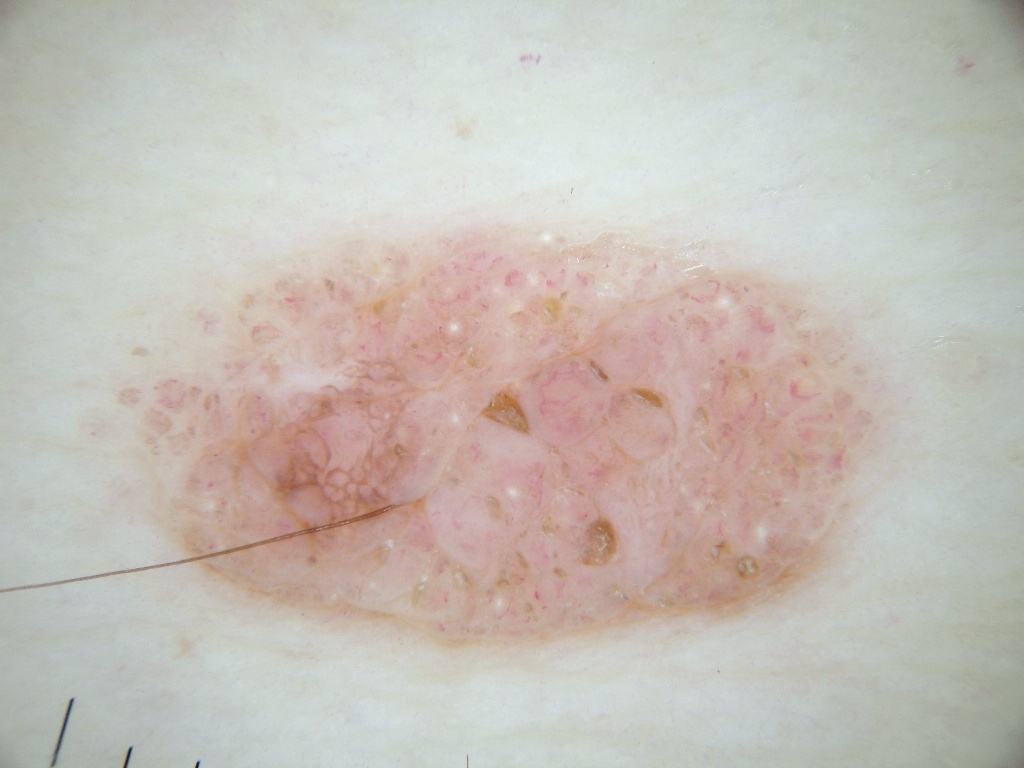subject — female, aged 63 to 67 | modality — dermoscopy of a skin lesion | dermoscopic findings — pigment network and milia-like cysts; absent: negative network, globules, and streaks | extent — ~38% of the field | location — <bbox>76, 197, 894, 661</bbox> | assessment — a melanocytic nevus, a benign lesion.